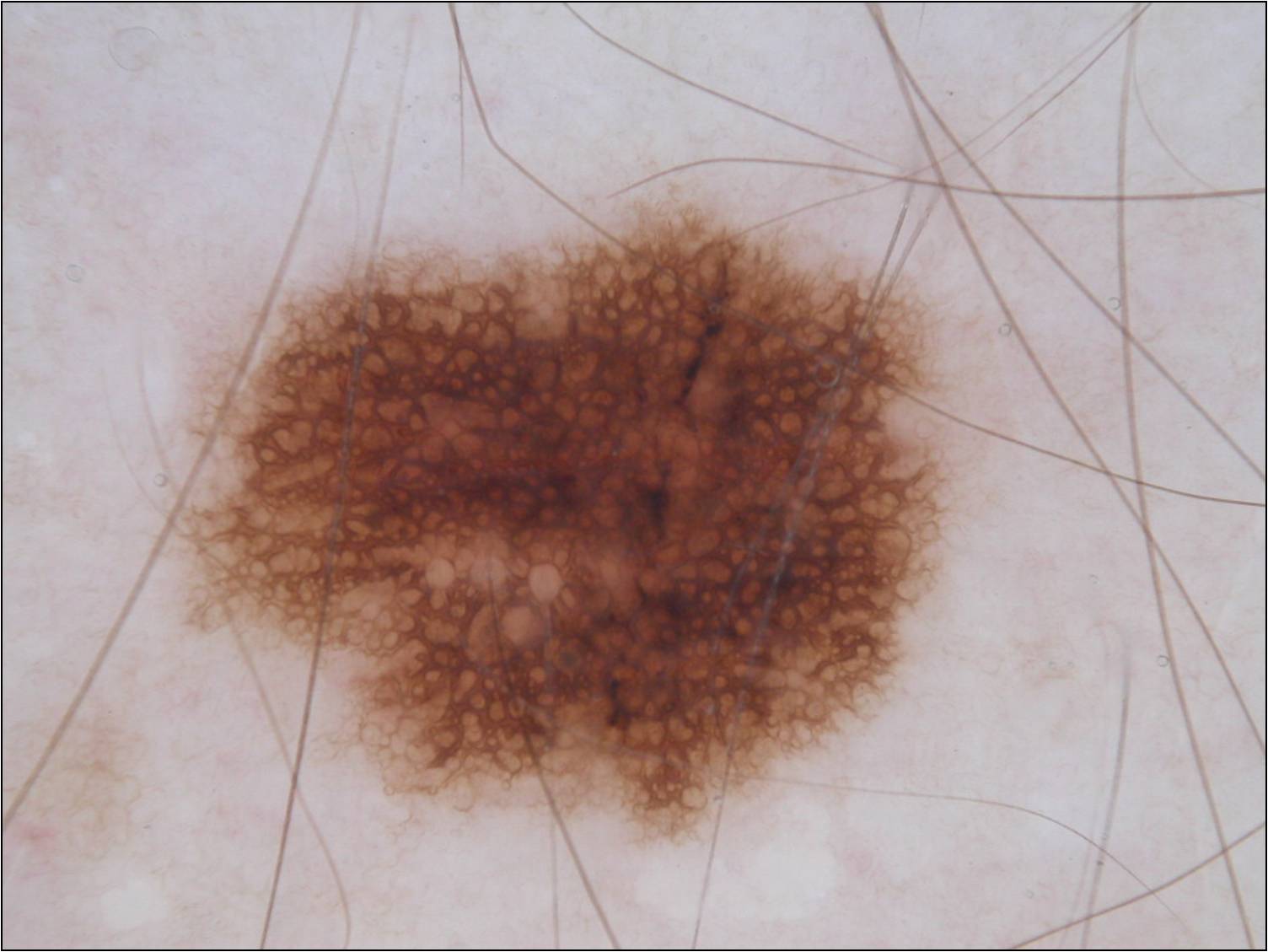modality = dermatoscopic image of a skin lesion; subject = female, aged 28 to 32; location = (177, 191, 962, 853); lesion extent = large; features = pigment network; impression = a melanocytic nevus.